A subject aged 67: 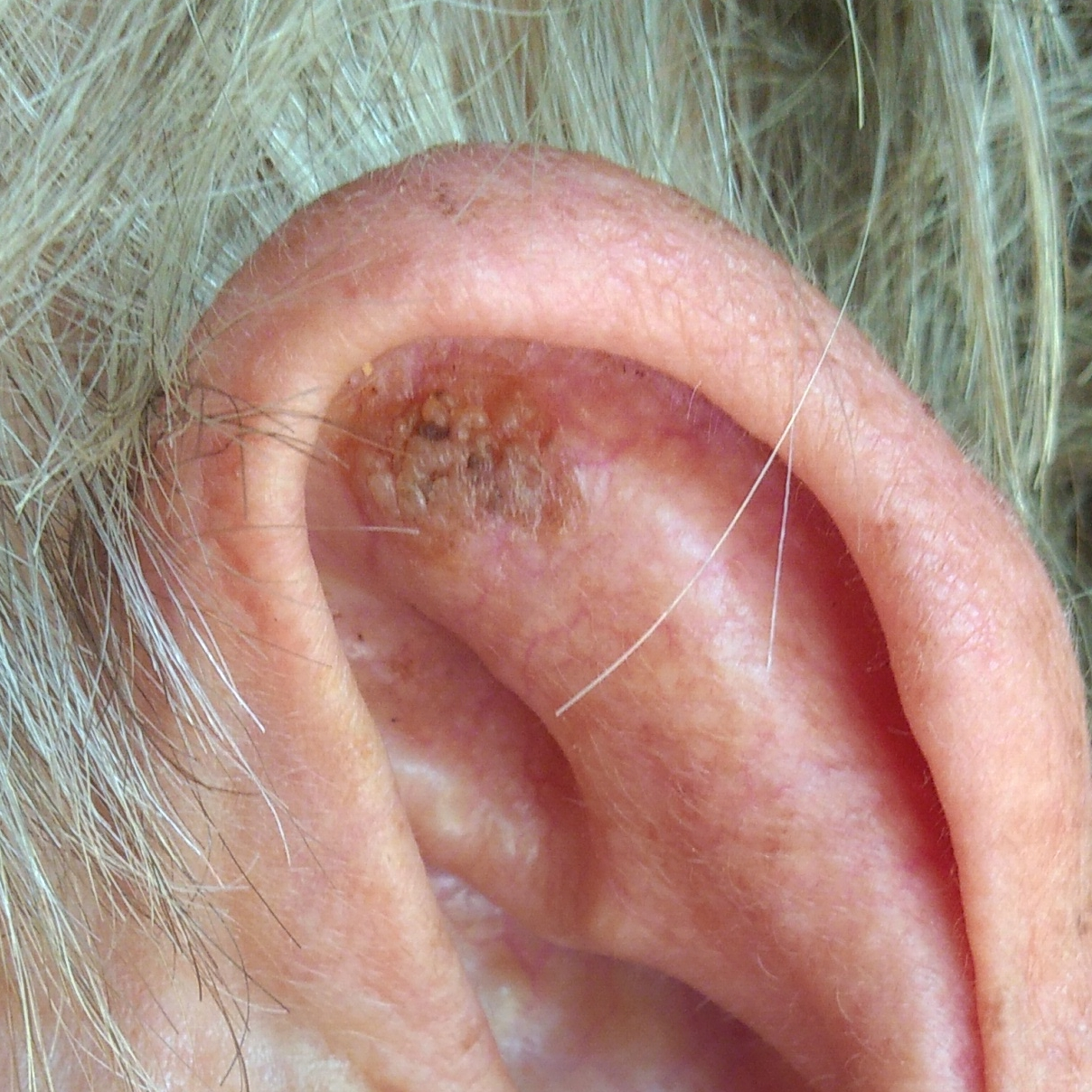The lesion was found on an ear. By the patient's account, the lesion is elevated and itches. Clinically diagnosed as a benign lesion — a seborrheic keratosis.